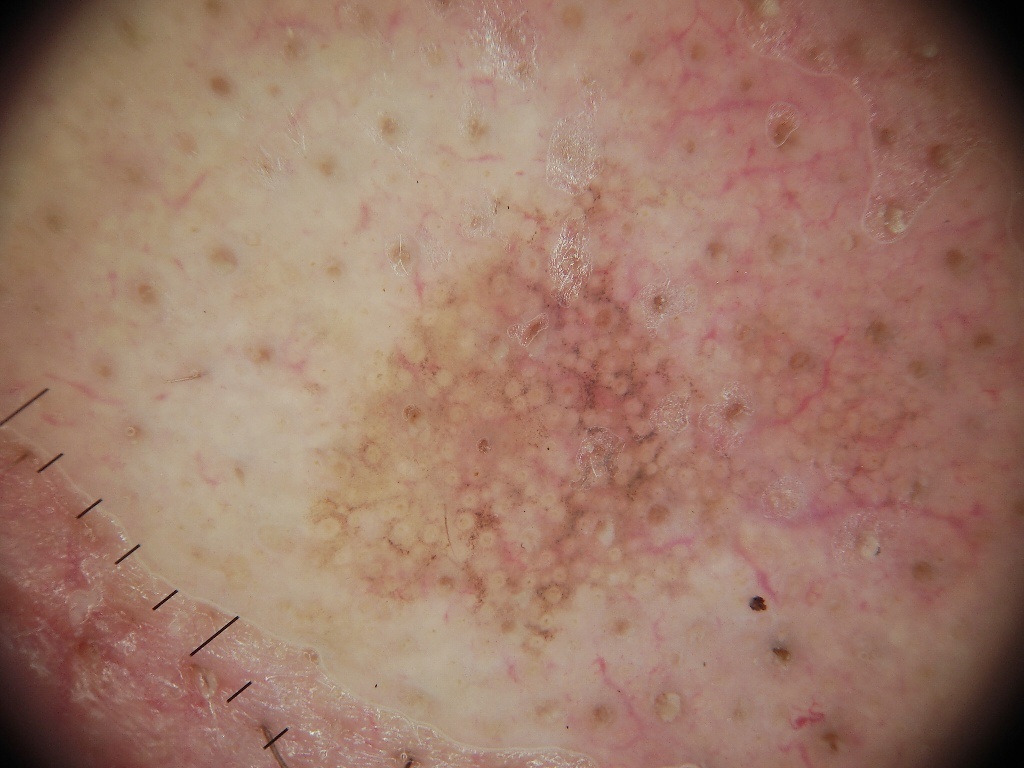A male patient aged approximately 80.
Dermoscopy of a skin lesion.
A moderately sized lesion.
Dermoscopically, the lesion shows no milia-like cysts, streaks, negative network, globules, or pigment network.
In (x1, y1, x2, y2) order, the lesion's extent is <bbox>288, 146, 746, 684</bbox>.
The biopsy diagnosis was a melanoma.